Dermoscopy of a skin lesion.
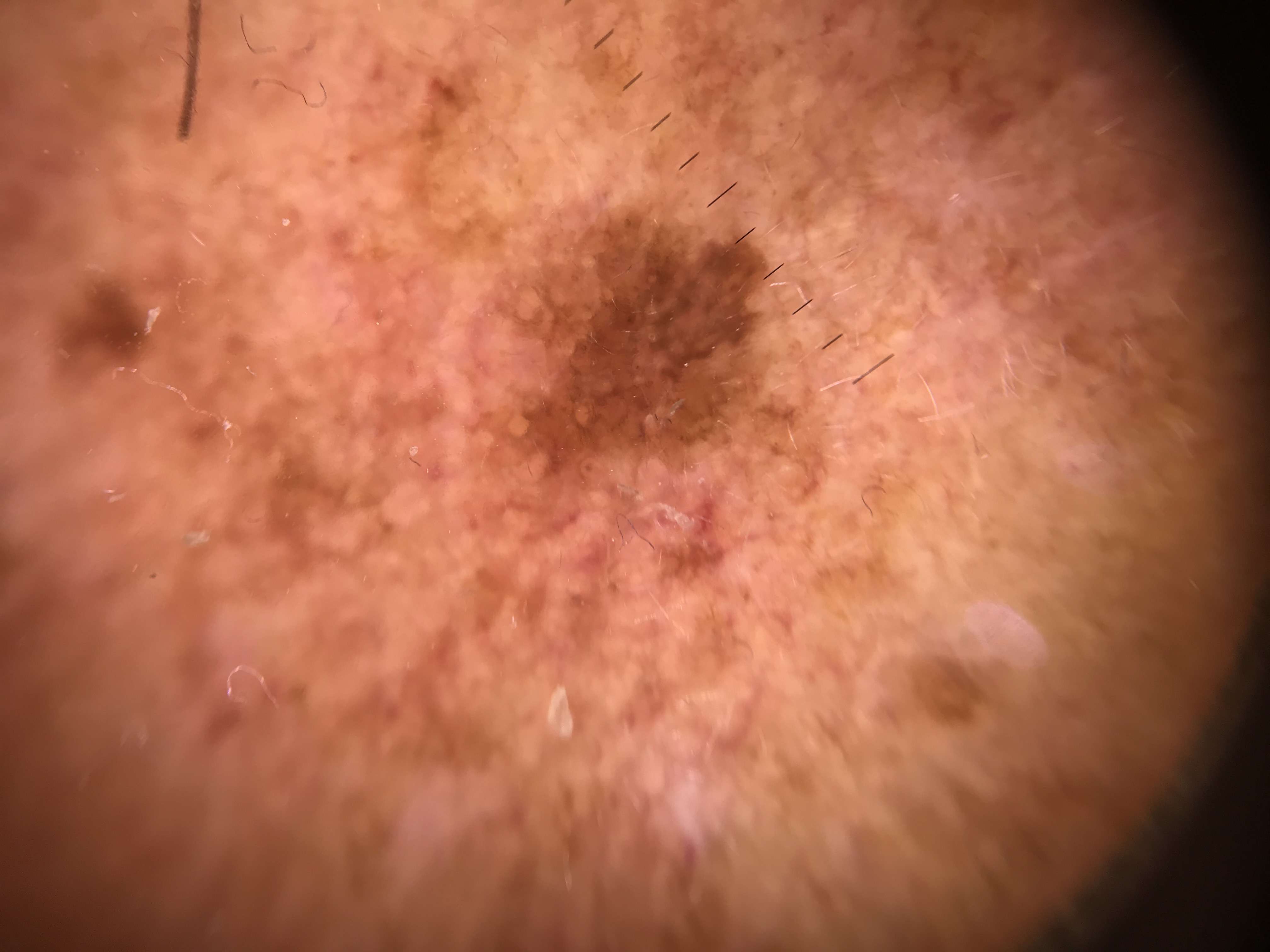assessment — seborrheic keratosis (expert consensus)